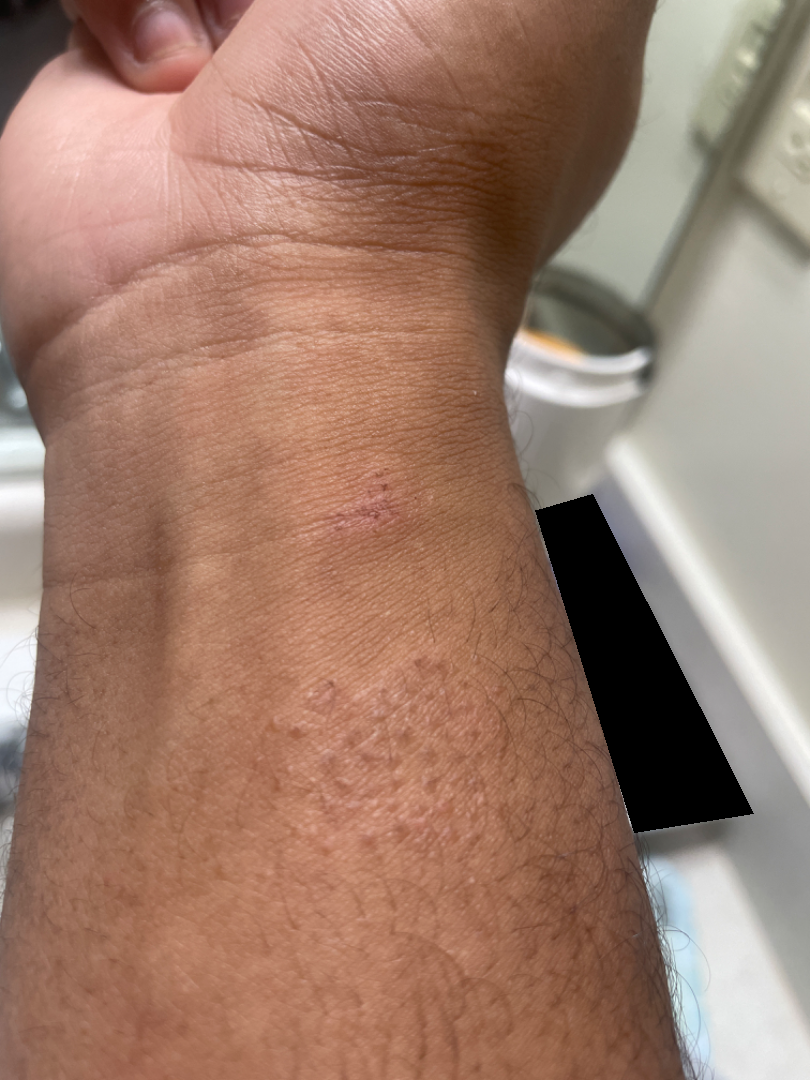Findings: Eczema (leading); Impetigo (considered); Allergic Contact Dermatitis (considered).